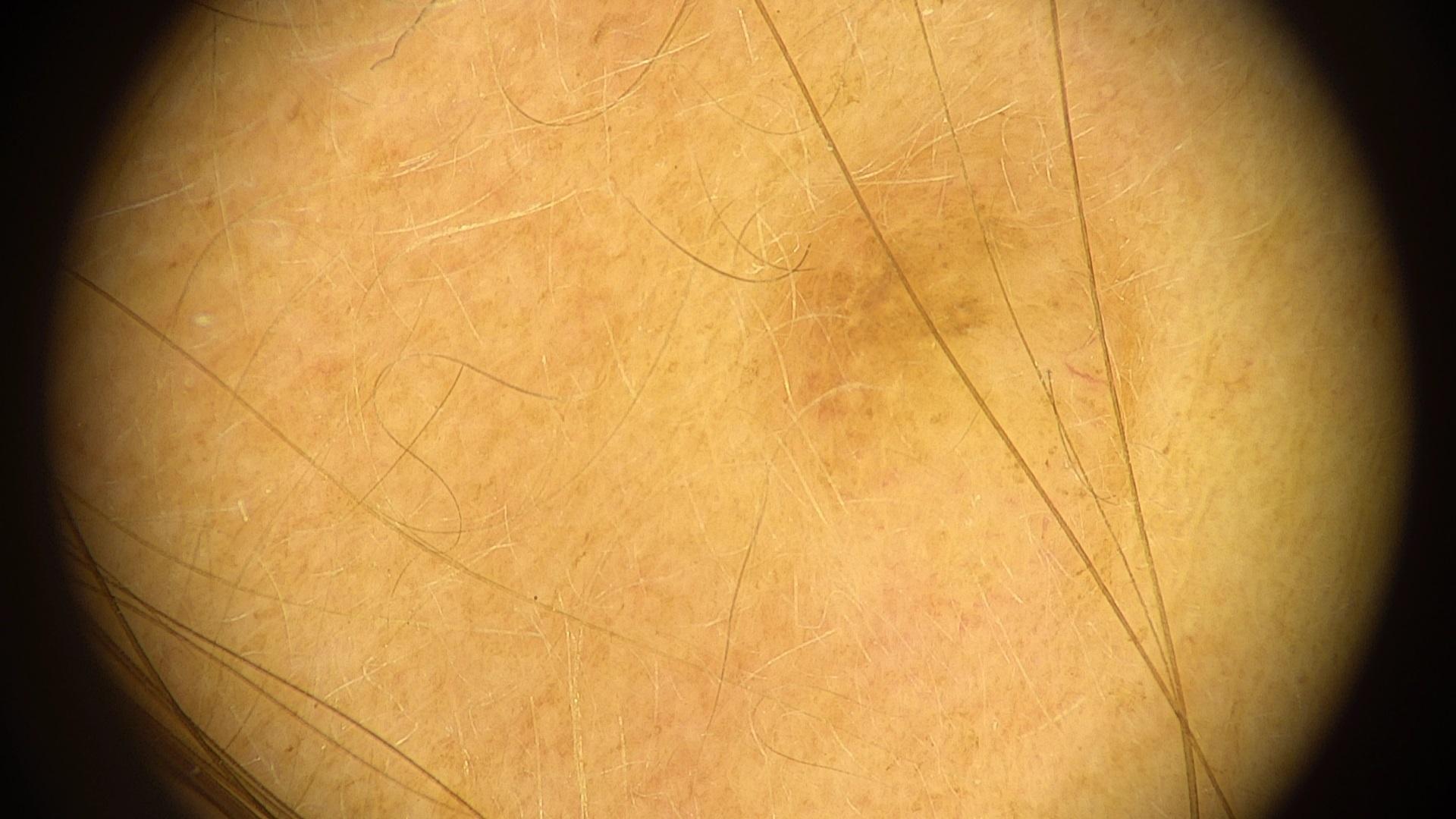| field | value |
|---|---|
| assessment | Nevus |